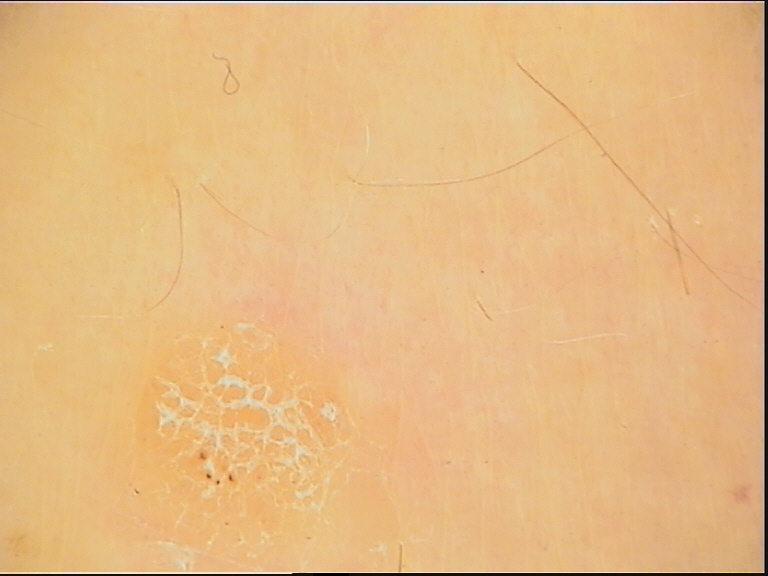Labeled as a keratinocytic lesion — a seborrheic keratosis.